The photograph was taken at an angle. The subject is 30–39, female. The lesion involves the palm — 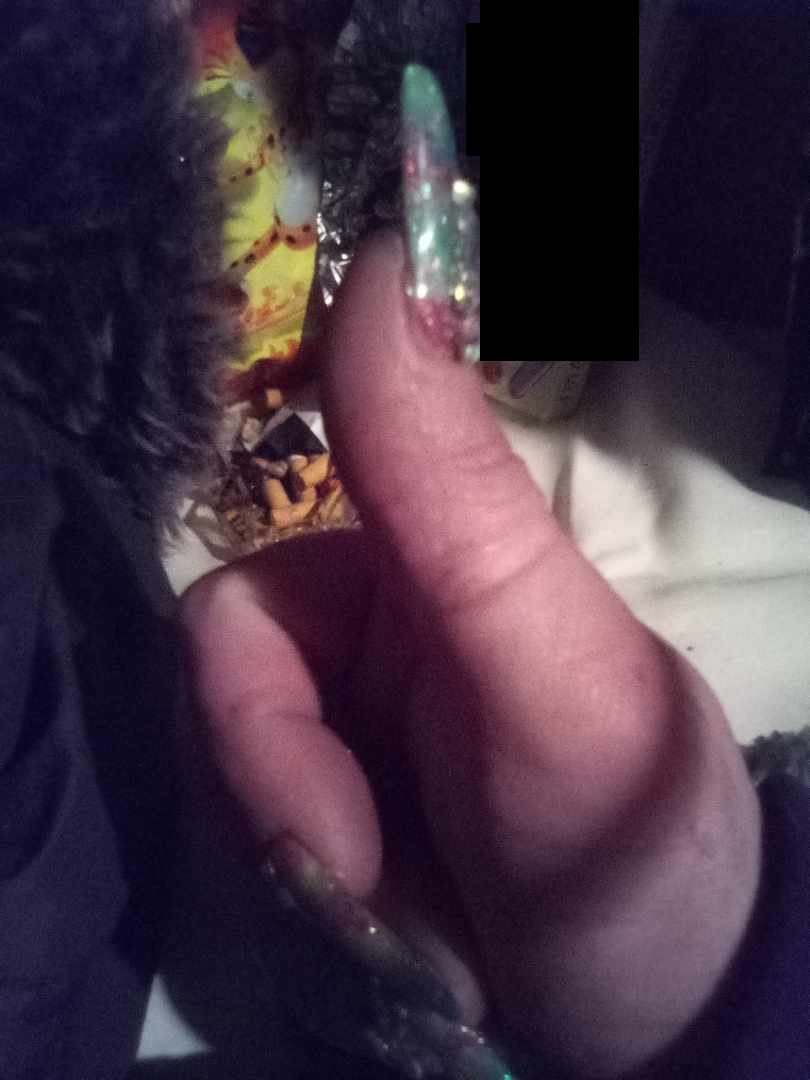assessment = could not be assessed | symptoms = itching | constitutional symptoms = none reported | skin tone = self-reported FST VI | described texture = raised or bumpy | patient describes the issue as = a rash.